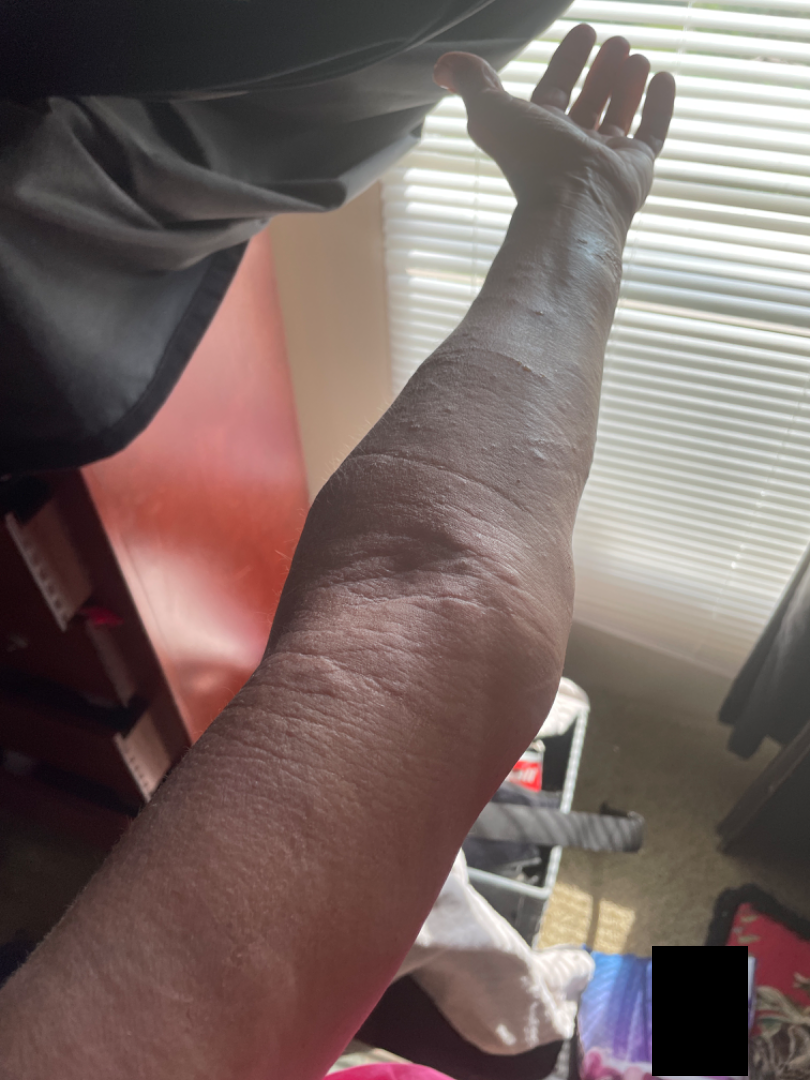An image taken at a distance.
Located on the head or neck, arm and back of the hand.
The reviewing dermatologist's impression was: the favored diagnosis is Allergic Contact Dermatitis; possibly Irritant Contact Dermatitis.